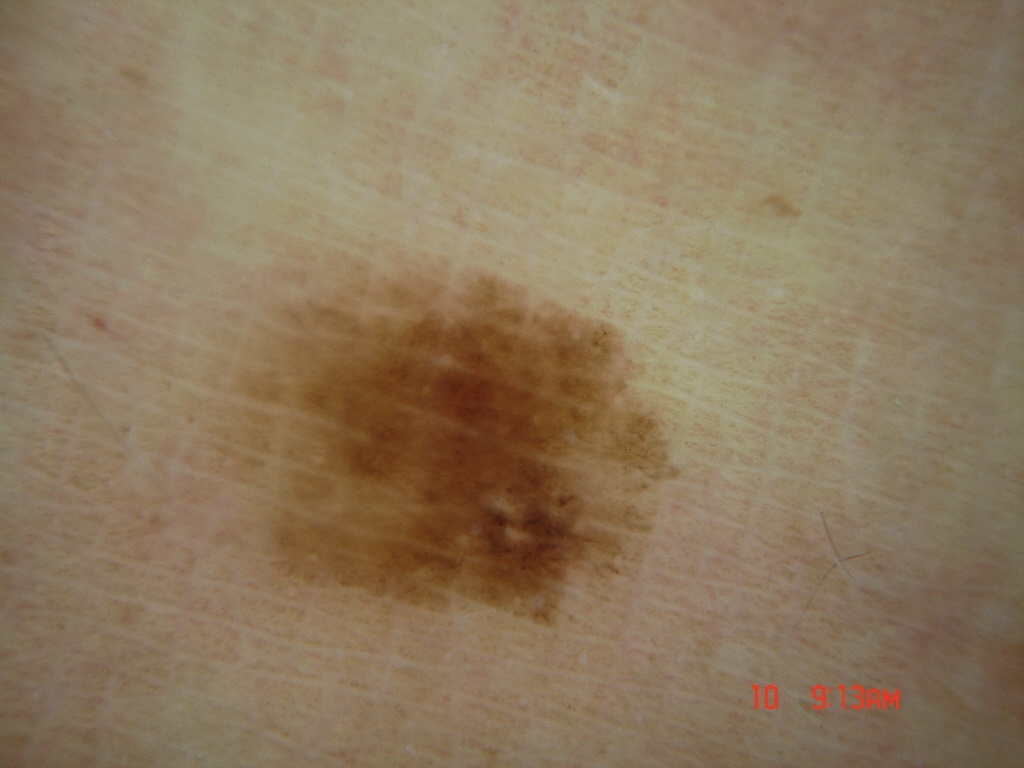subject: female, aged 13 to 17; image: dermoscopic image; lesion extent: moderate; features: pigment network; lesion location: 174, 244, 696, 639; impression: a melanocytic nevus.